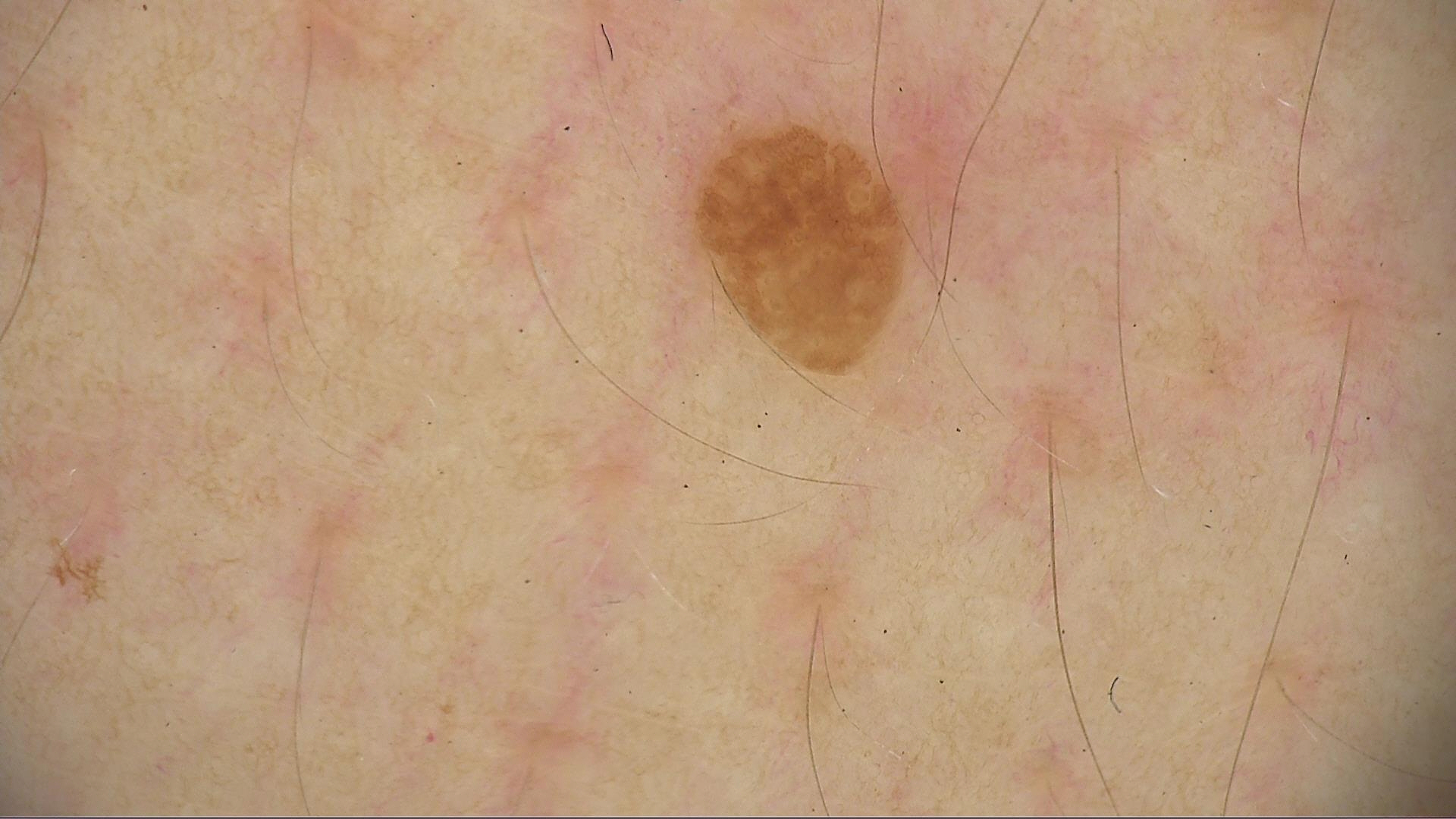A dermatoscopic image of a skin lesion. Consistent with a keratinocytic lesion — a seborrheic keratosis.